A dermoscopic close-up of a skin lesion. A male patient, about 45 years old: 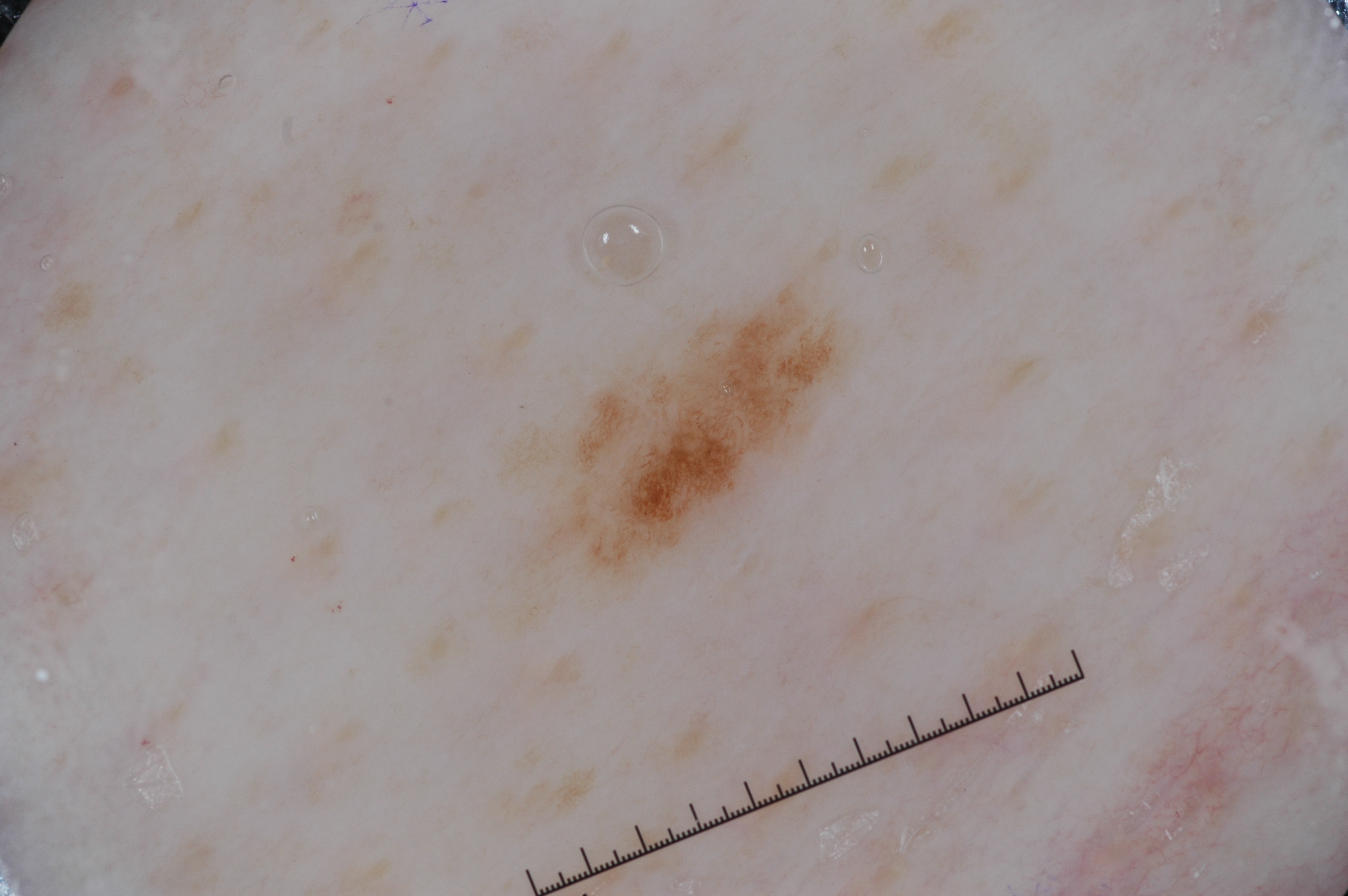A small lesion within a wider field of skin. With coordinates (x1, y1, x2, y2), the lesion occupies the region 537/294/842/581. Dermoscopic review identifies pigment network; no streaks, milia-like cysts, or negative network. Expert review diagnosed this as a melanocytic nevus, a benign lesion.